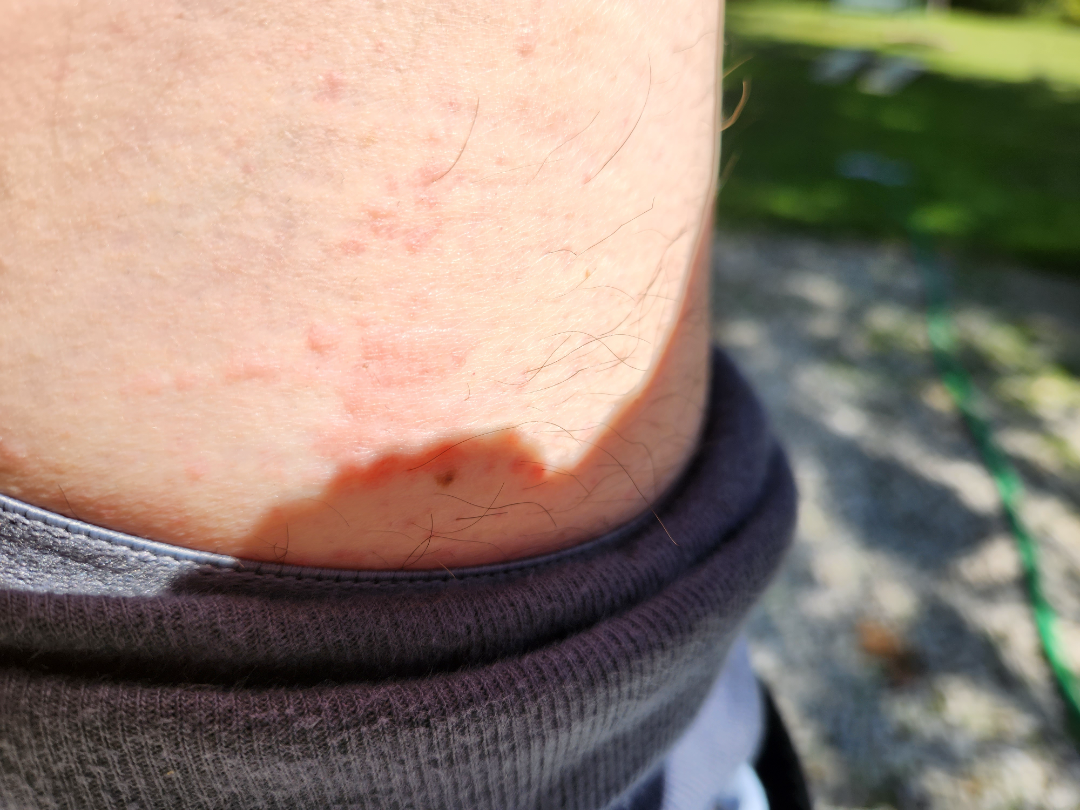  assessment: unable to determine
  patient: male, age 60–69
  shot_type: close-up
  texture: raised or bumpy
  body_site: leg
  duration: three to twelve months
  patient_category: a rash
  symptoms: none reported